This is a dermoscopic photograph of a skin lesion:
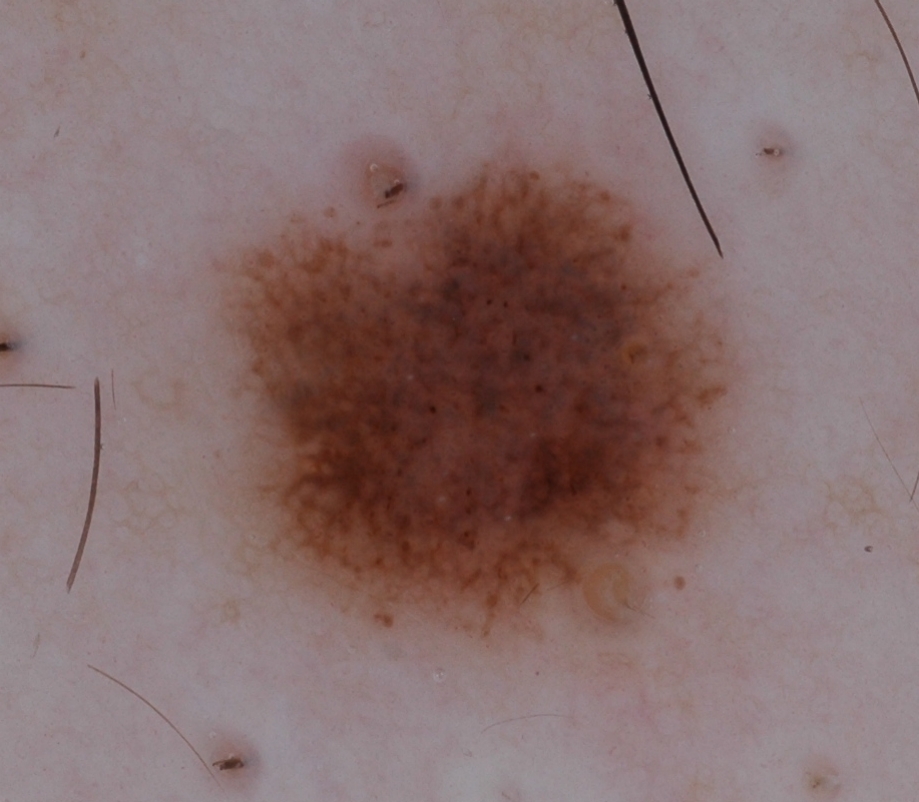Dermoscopically, the lesion shows pigment network and globules.
In (x1, y1, x2, y2) order, the lesion spans [197, 144, 749, 646].
Expert review diagnosed this as a melanocytic nevus, a benign lesion.